Located on the leg; an image taken at an angle; female contributor, age 30–39:
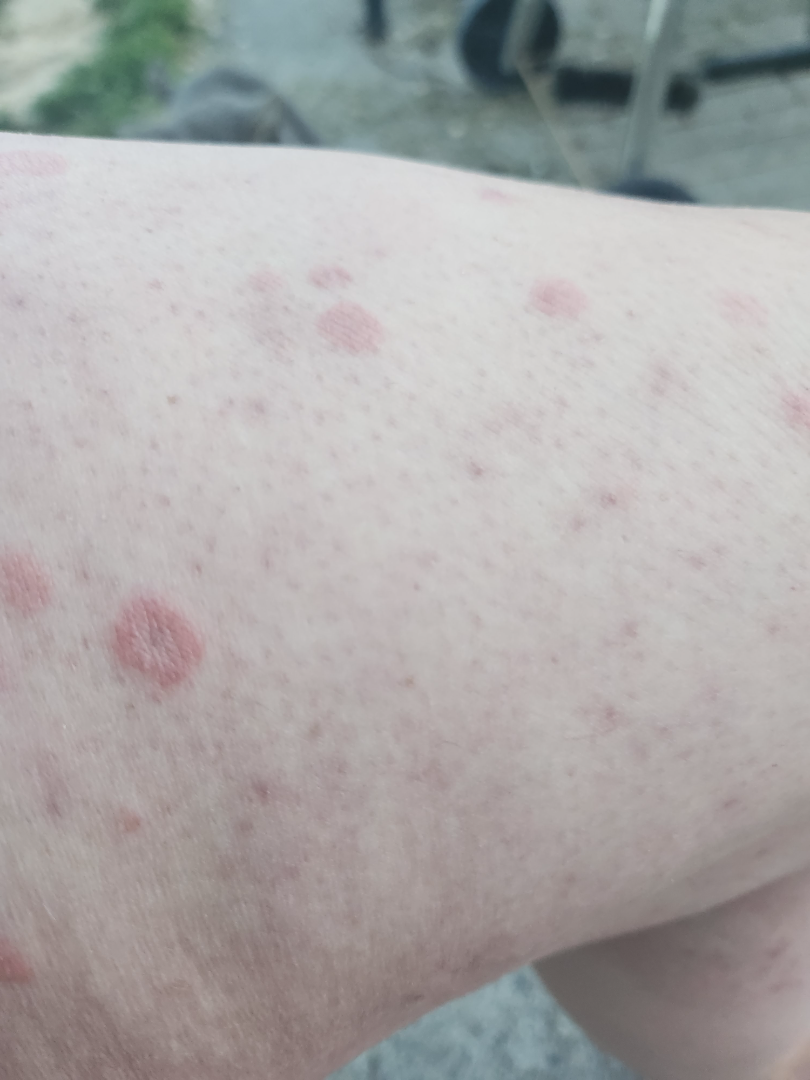Present for more than one year. Symptoms reported: itching. The patient considered this a rash. No relevant systemic symptoms. A single dermatologist reviewed the case: most likely Psoriasis; possibly Eczema; also on the differential is Pityriasis rosea.